A dermatoscopic image of a skin lesion:
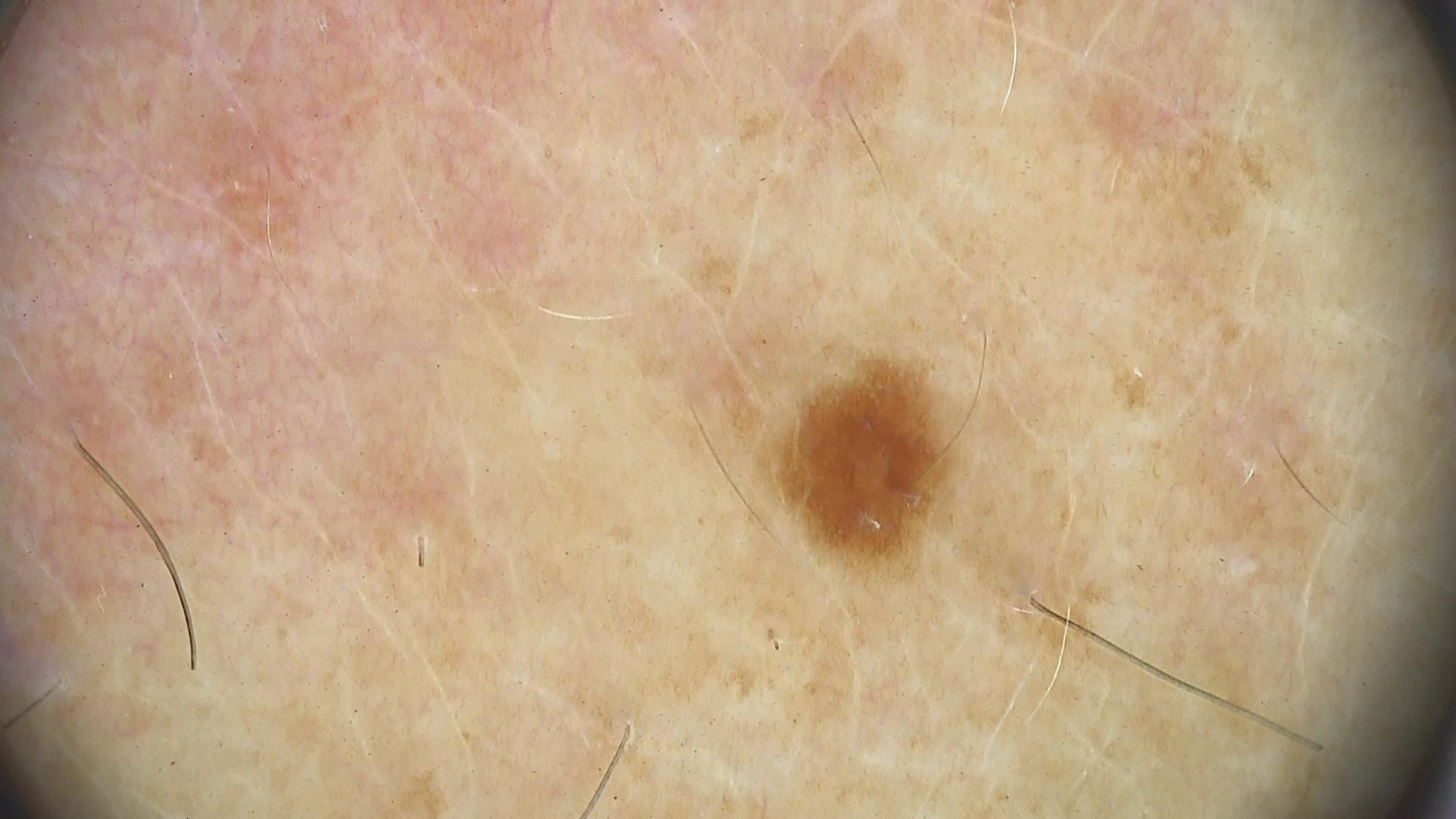Summary: The morphology is that of a banal lesion. Impression: The diagnostic label was a junctional nevus.